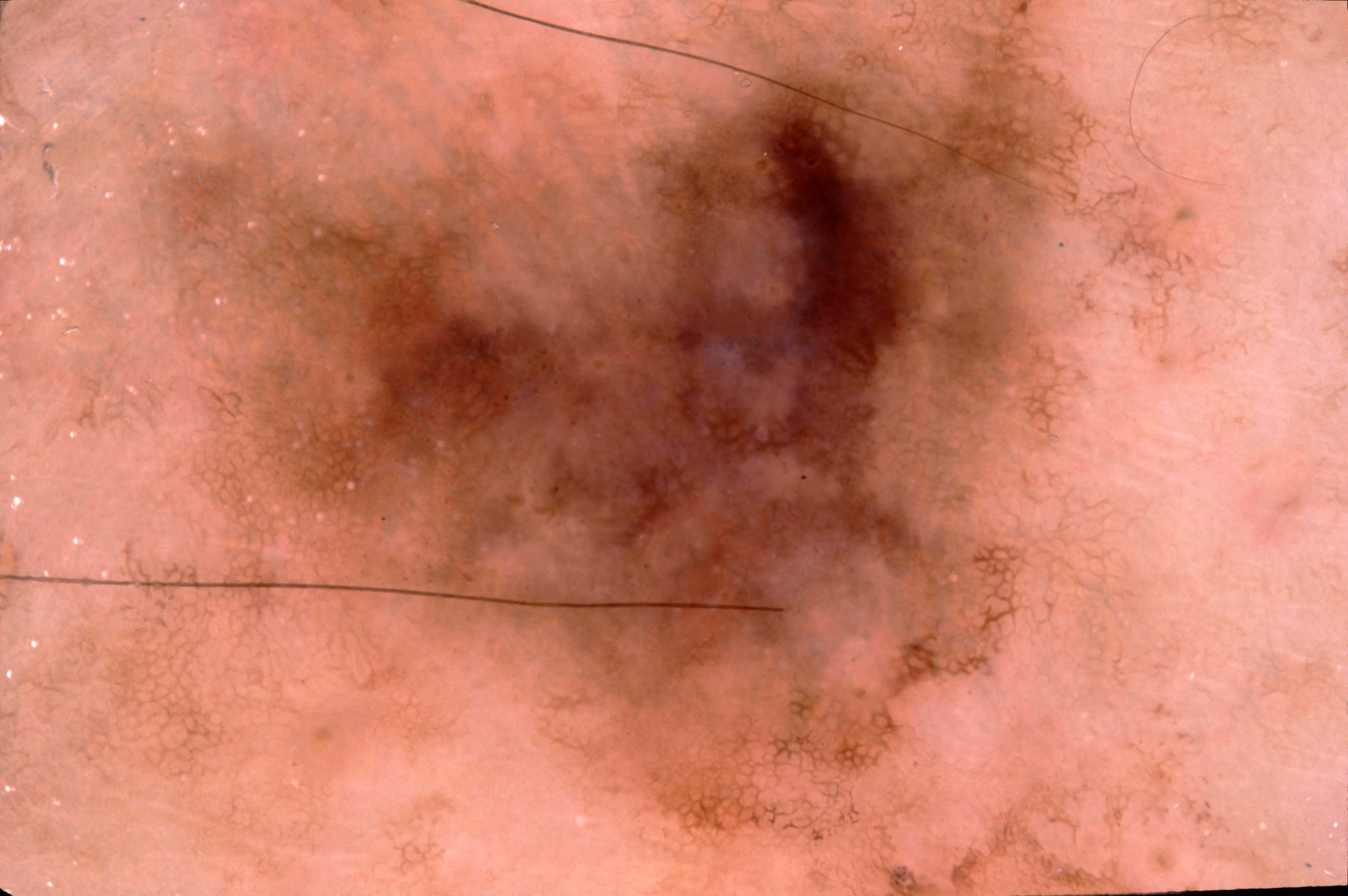Findings: Dermoscopy of a skin lesion. The lesion spans x1=169, y1=28, x2=1095, y2=840. The lesion takes up a large portion of the image. On dermoscopy, the lesion shows pigment network; no milia-like cysts, negative network, or streaks. Diagnosis: Histopathology confirmed a melanoma.